A dermoscopic close-up of a skin lesion · a female patient, aged 73 to 77:
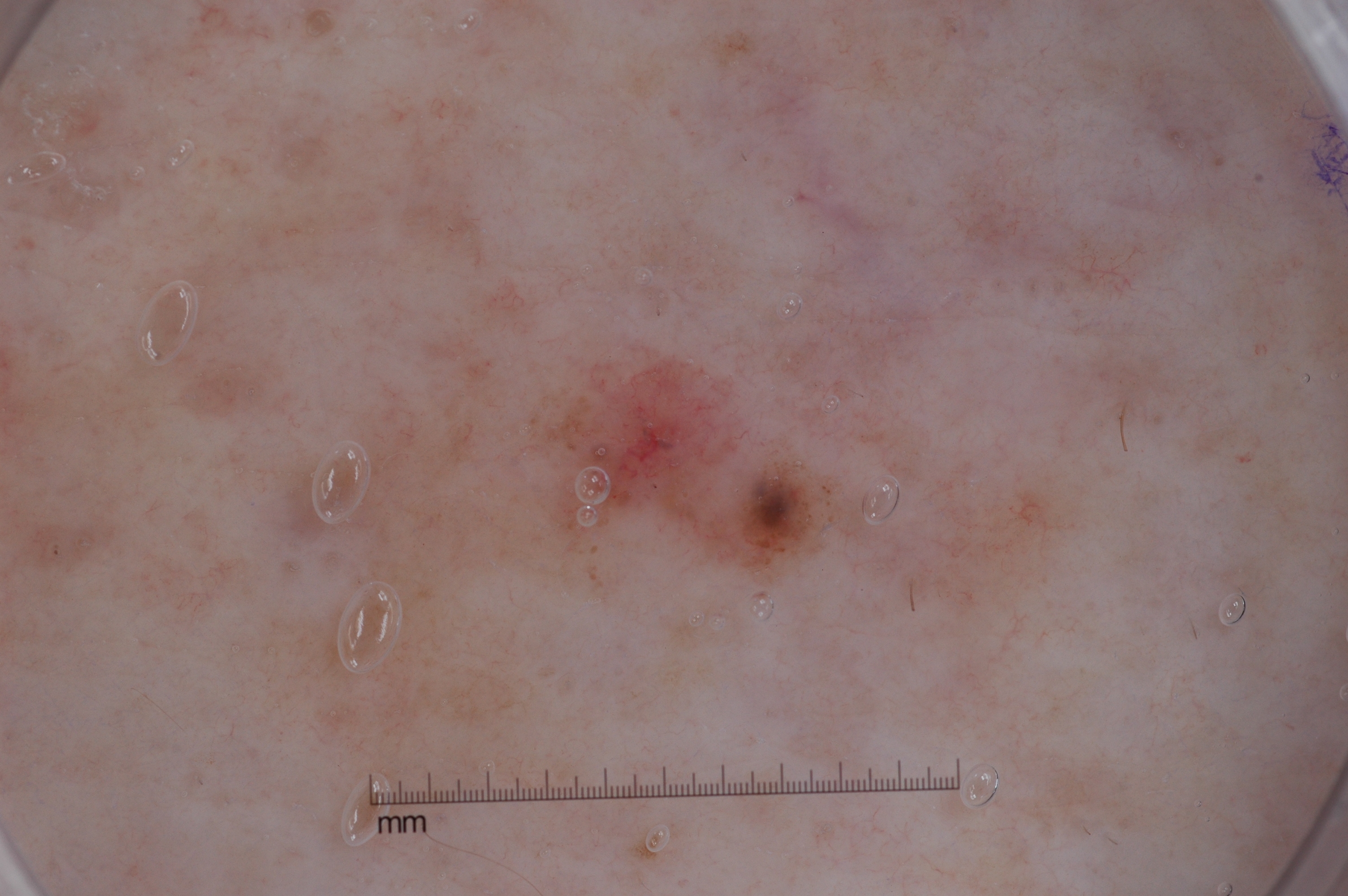<dermoscopy>
<lesion_location>
  <bbox_xyxy>493, 335, 857, 609</bbox_xyxy>
</lesion_location>
<dermoscopic_features>
  <present/>
  <absent>pigment network, milia-like cysts, negative network, streaks</absent>
</dermoscopic_features>
<lesion_extent>
  <approx_field_fraction_pct>6</approx_field_fraction_pct>
</lesion_extent>
<diagnosis>
  <name>melanoma</name>
  <malignancy>malignant</malignancy>
  <lineage>melanocytic</lineage>
  <provenance>histopathology</provenance>
</diagnosis>
</dermoscopy>